Located on the front of the torso, leg, back of the torso and head or neck · this is a close-up image: 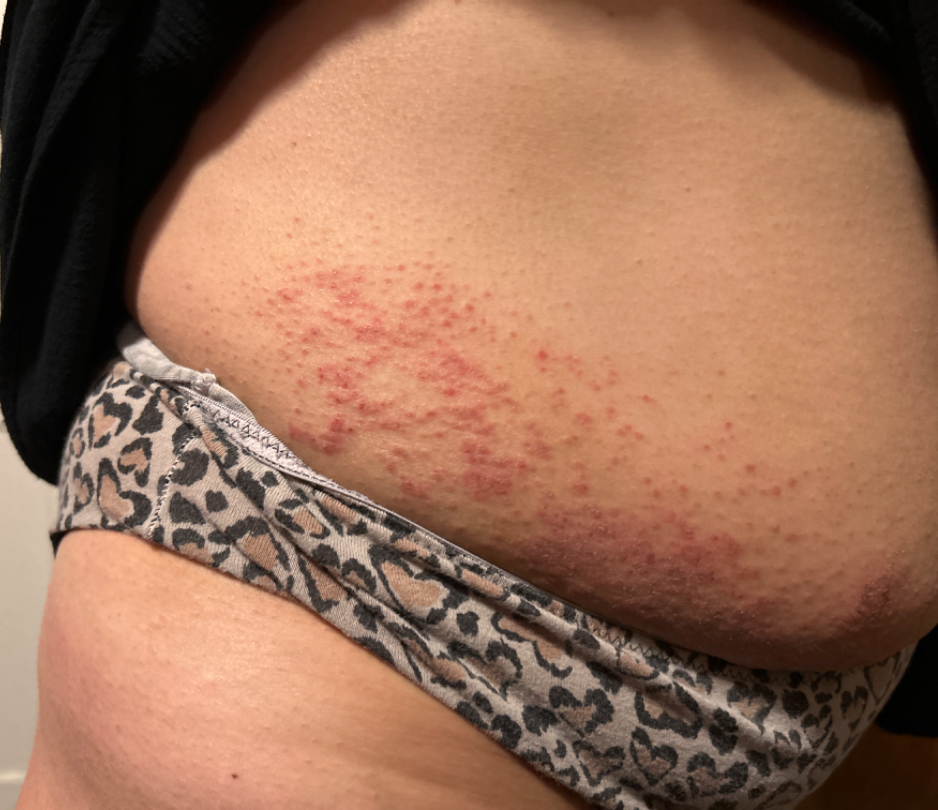{
  "duration": "one to three months",
  "patient_category": "a rash",
  "symptoms": [
    "bothersome appearance",
    "itching",
    "darkening",
    "enlargement"
  ],
  "systemic_symptoms": "none reported",
  "skin_tone": {
    "fitzpatrick": "III",
    "monk_skin_tone": [
      3,
      4
    ]
  },
  "differential": {
    "leading": [
      "Eczema"
    ]
  }
}